Close-up view; self-categorized by the patient as a rash; present for one to four weeks; the lesion is associated with bothersome appearance; female patient, age 18–29 — 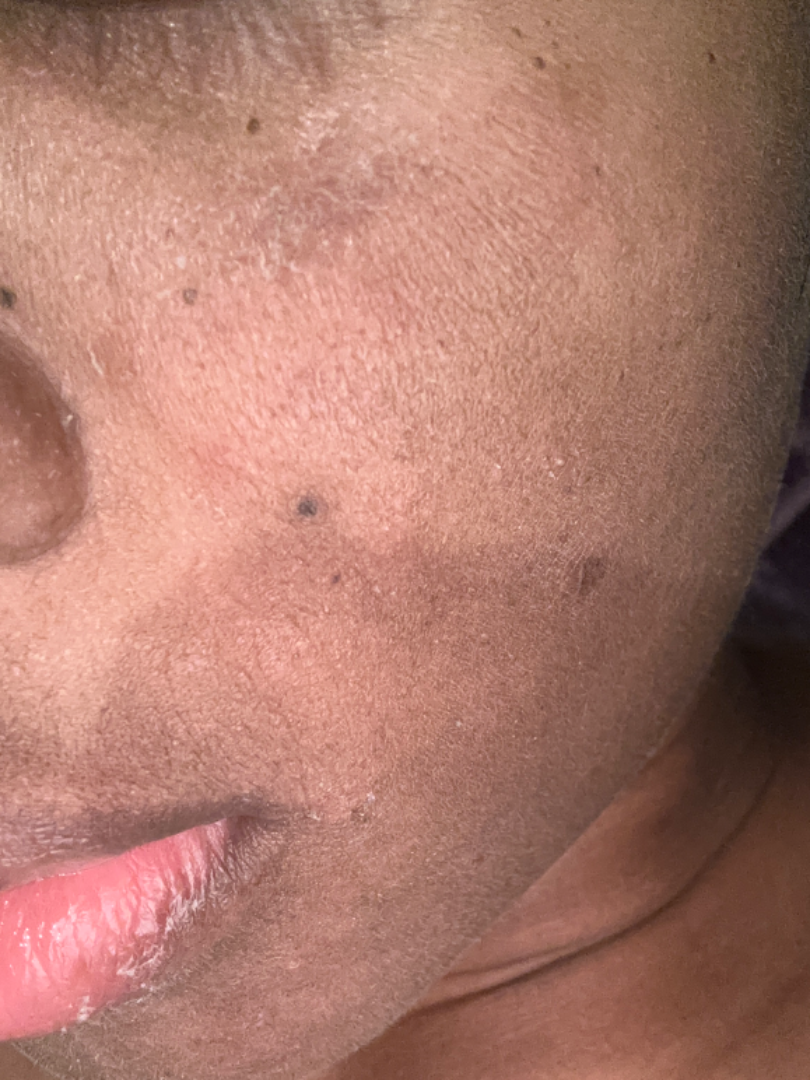Diagnostic features were not clearly distinguishable in this photograph.